The contributor notes the condition has been present for one to four weeks. The lesion involves the head or neck. The contributor notes the lesion is raised or bumpy. An image taken at an angle. No associated systemic symptoms reported. The patient described the issue as a rash. The subject is 18–29, female. Reported lesion symptoms include enlargement — 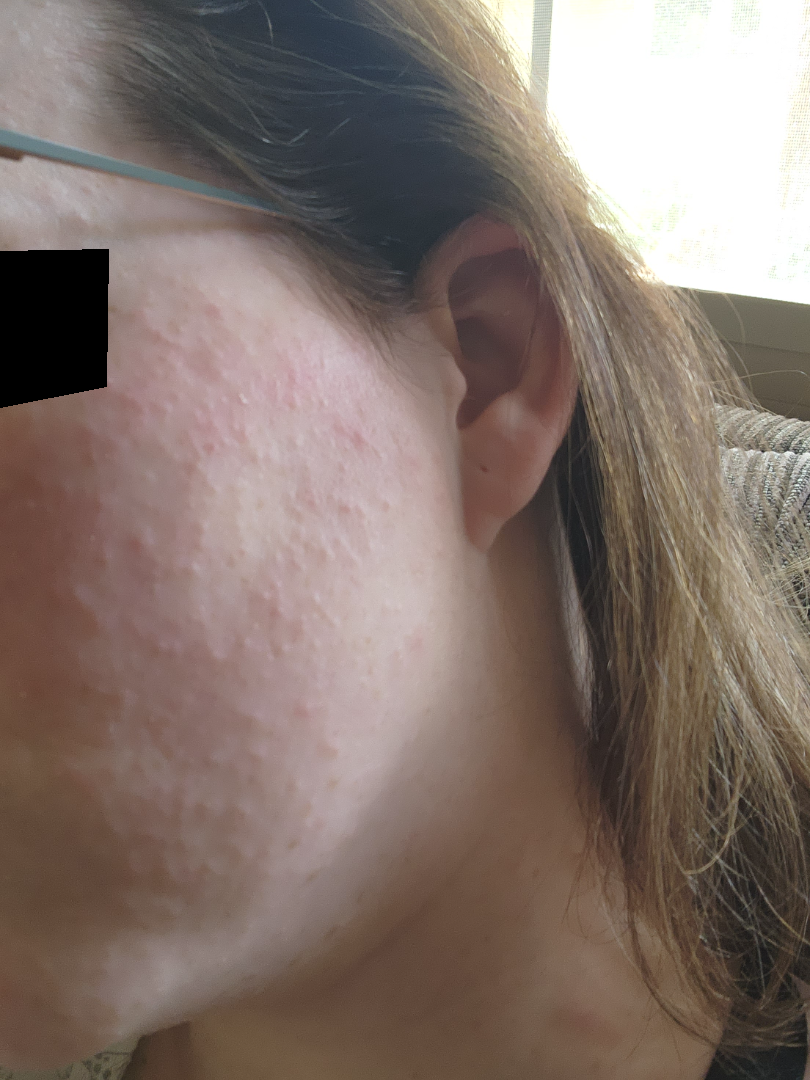On photographic review: favoring Rosacea; with consideration of Allergic Contact Dermatitis; less probable is Acne; less likely is Miliaria; lower on the differential is Folliculitis.